A skin lesion imaged with a dermatoscope — 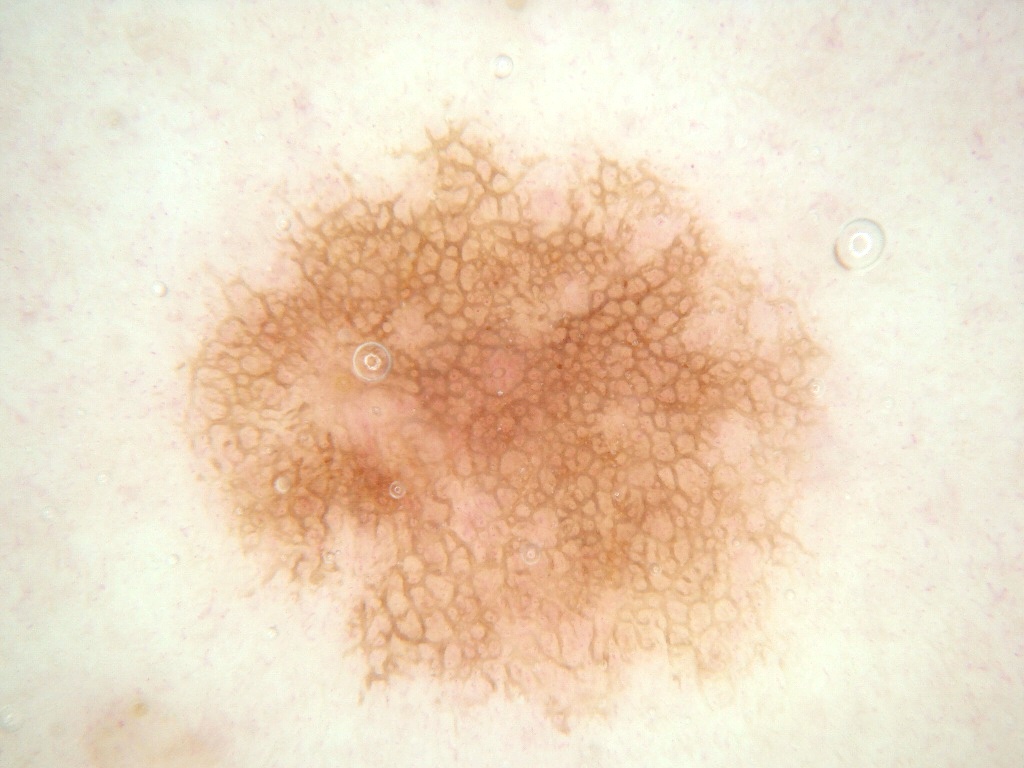In (x1, y1, x2, y2) order, the lesion is located at 164/115/841/733.
Diagnosed as a melanocytic nevus.